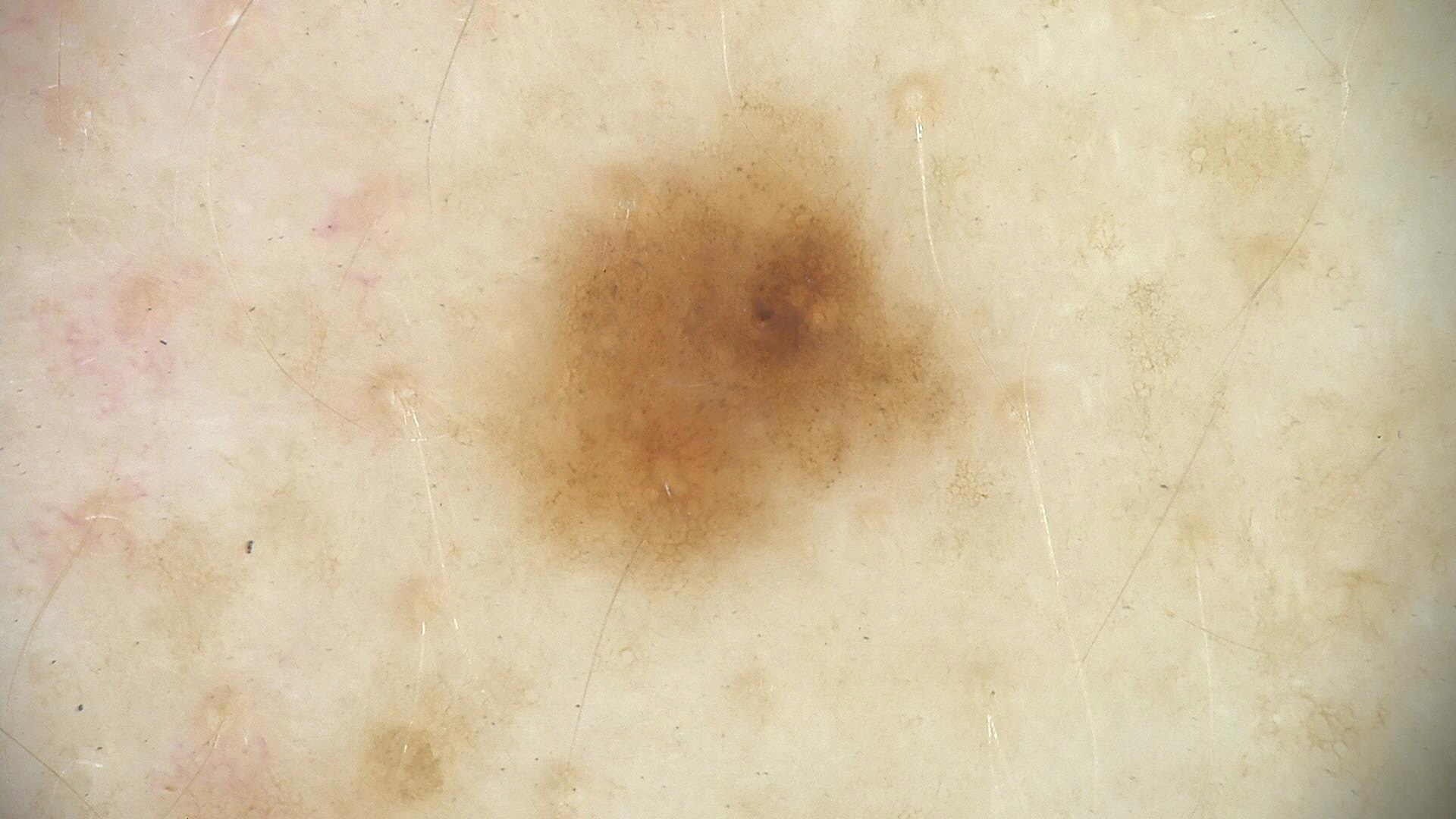Labeled as a dysplastic junctional nevus.